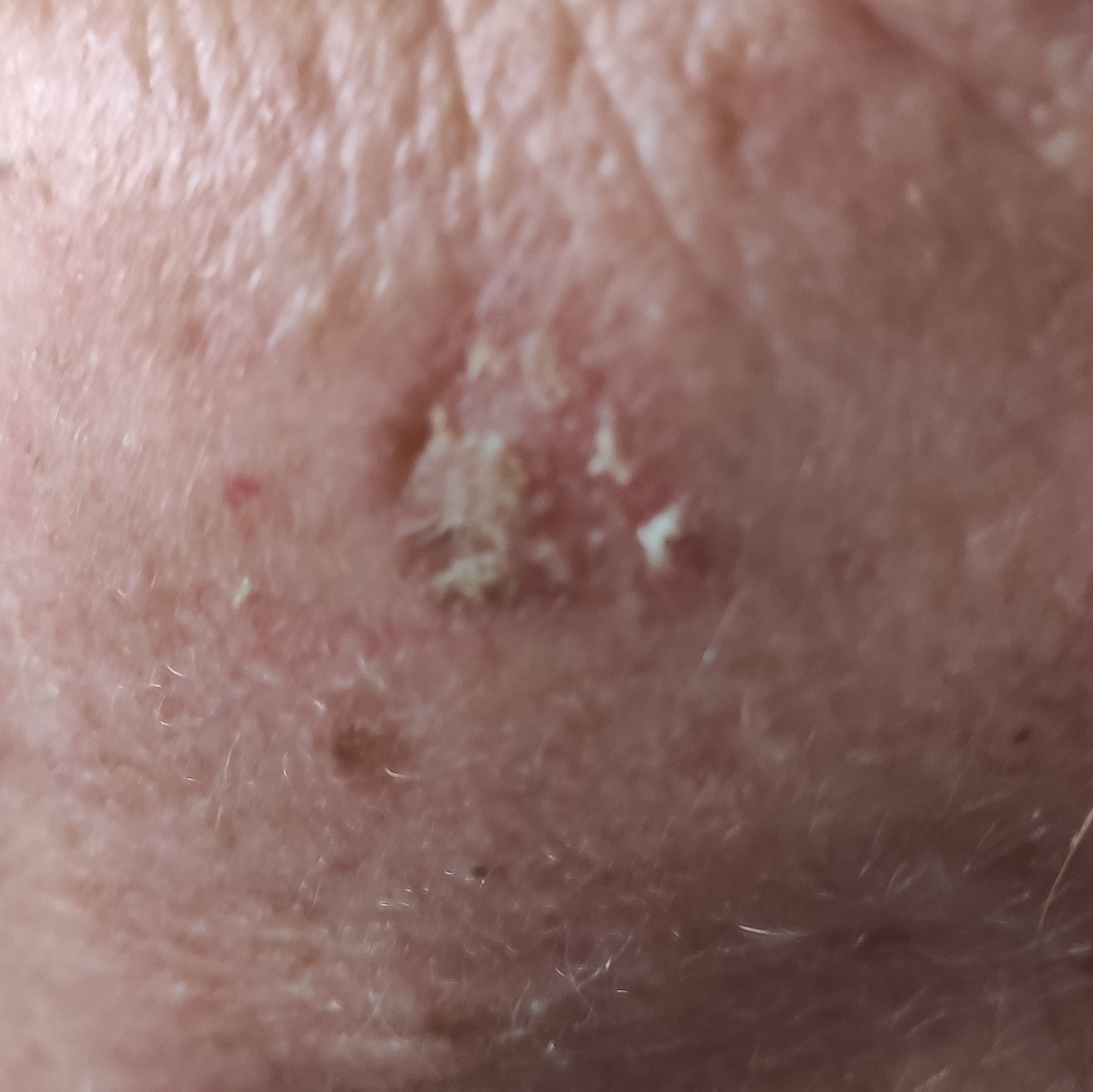A clinical photograph showing a skin lesion. A subject aged 69. The lesion is located on the face. Per patient report, the lesion has grown, has changed, and itches. The consensus clinical diagnosis was a lesion with uncertain malignant potential — an actinic keratosis.